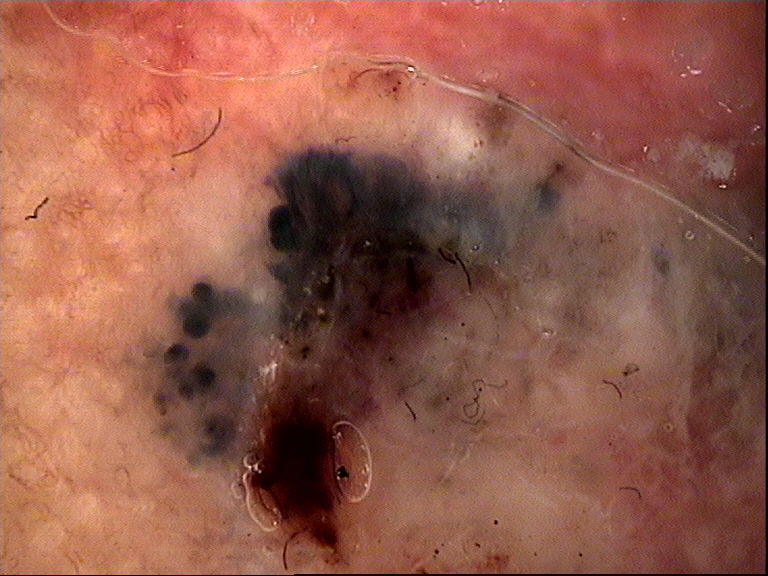Case:
- image type — dermatoscopy
- category — keratinocytic
- pathology — basal cell carcinoma (biopsy-proven)